This is a close-up image: 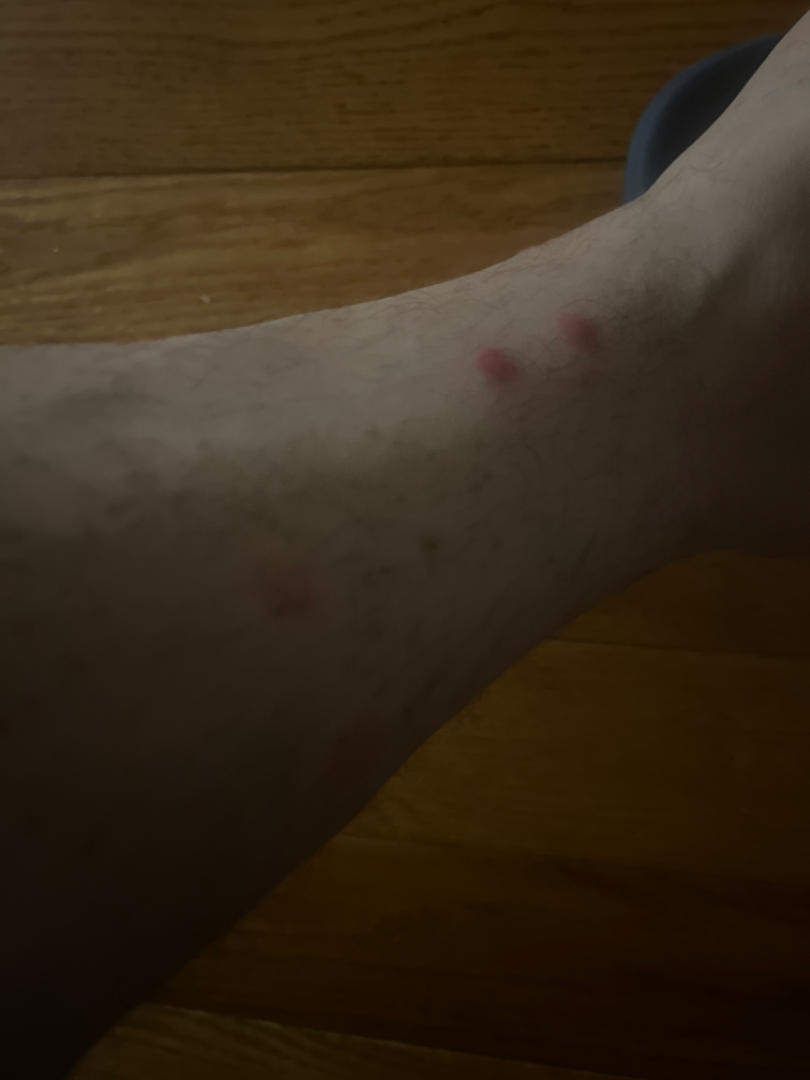Impression: No differential diagnosis could be assigned on photographic review.